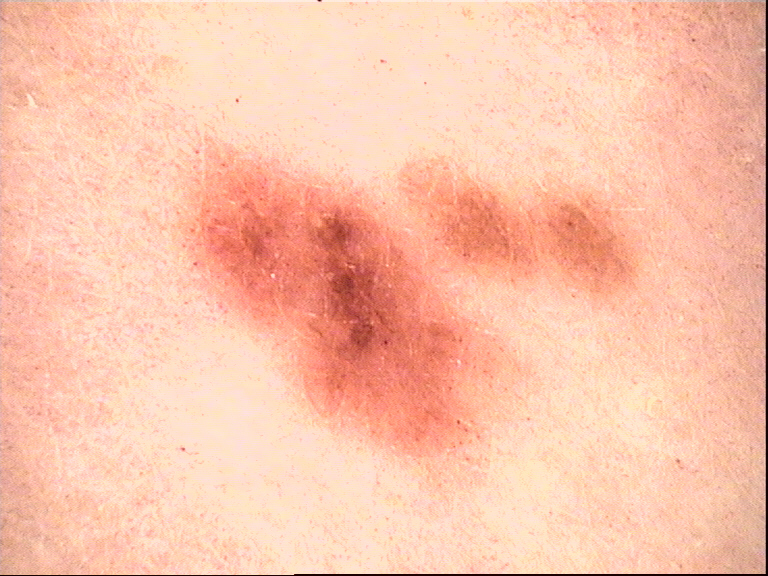class=dysplastic junctional nevus (expert consensus)